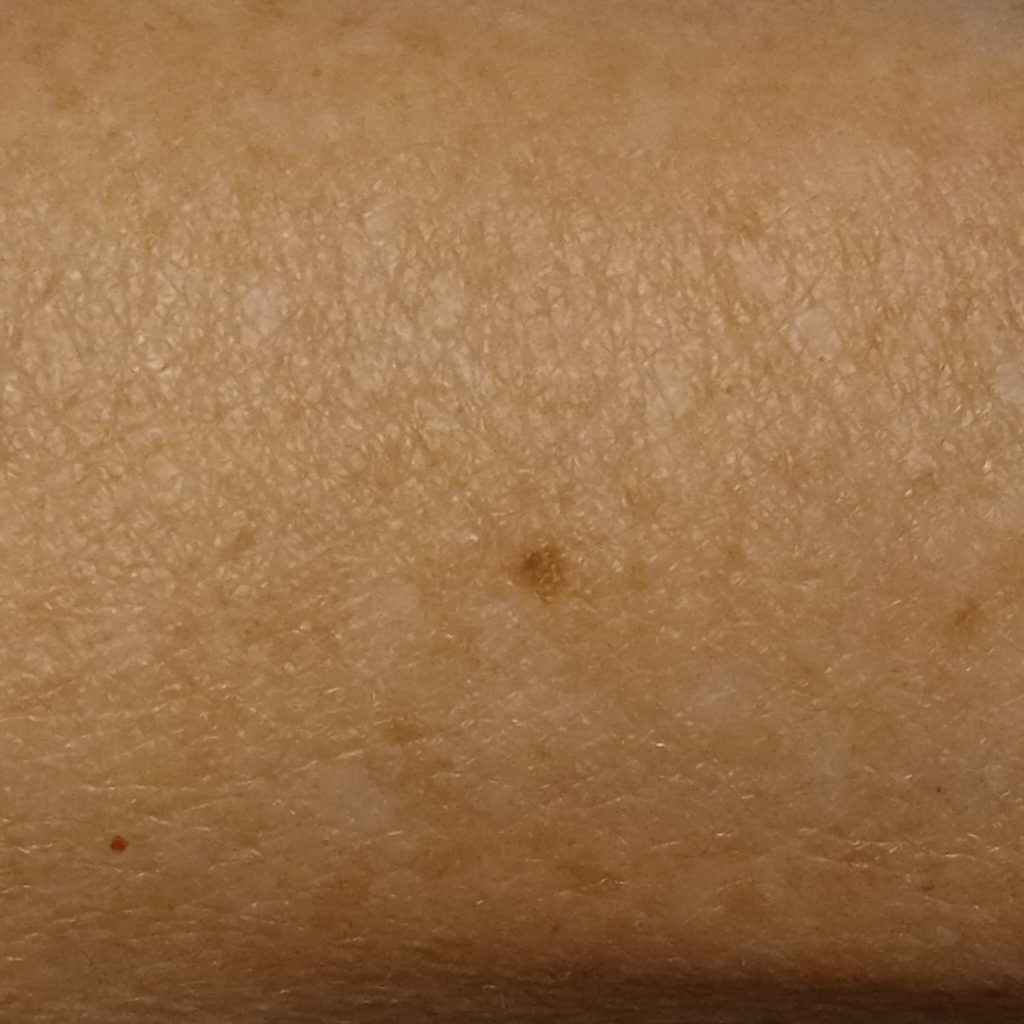{"image": "clinical photo", "mole_burden": "few melanocytic nevi overall", "referral": "research study (no referral diagnosis)", "sun_reaction": "skin tans without first burning", "lesion_location": "an arm", "lesion_size": {"diameter_mm": 2.1}, "diagnosis": {"name": "melanocytic nevus", "malignancy": "benign"}}